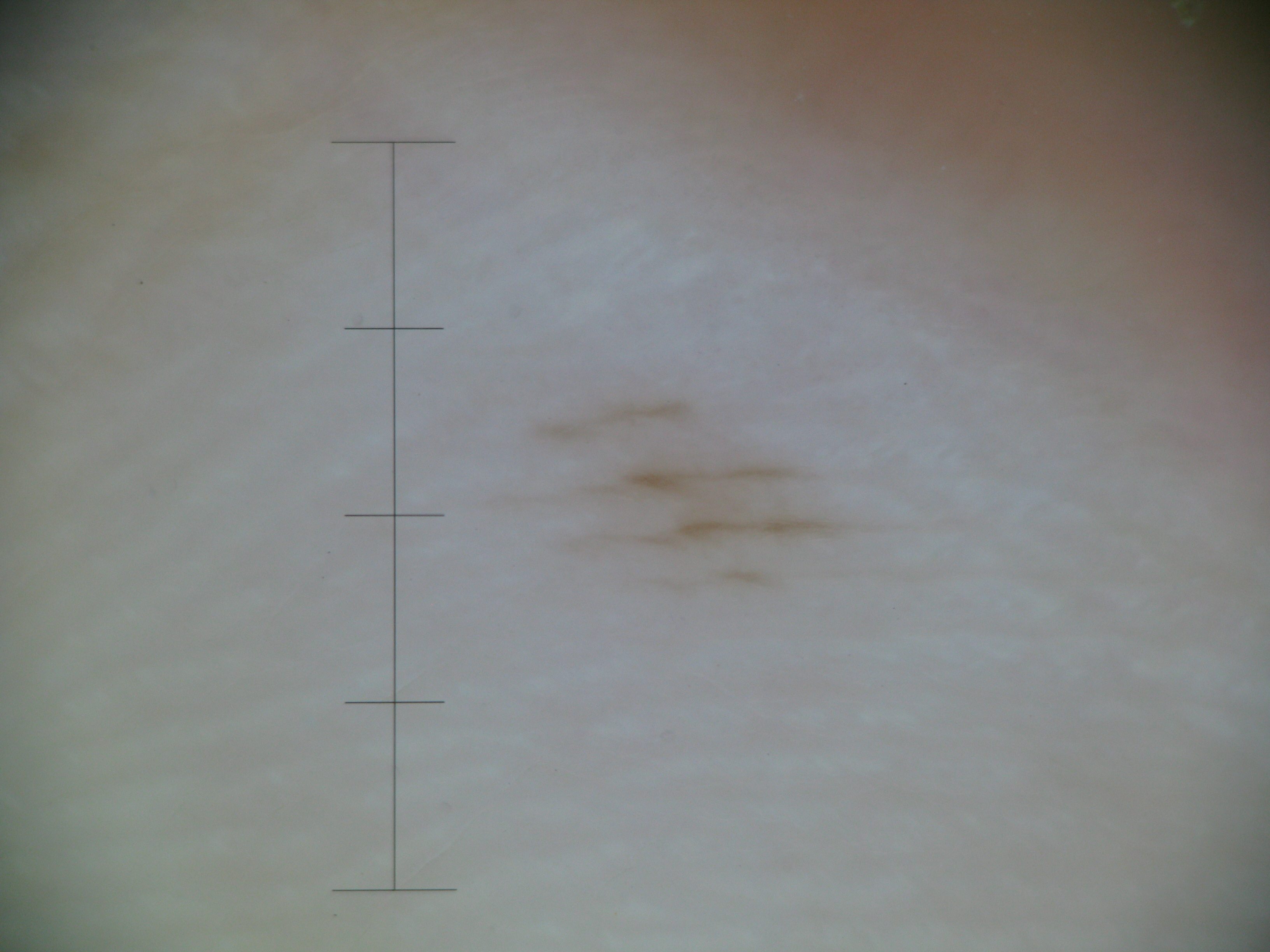Conclusion:
Diagnosed as an acral junctional nevus.